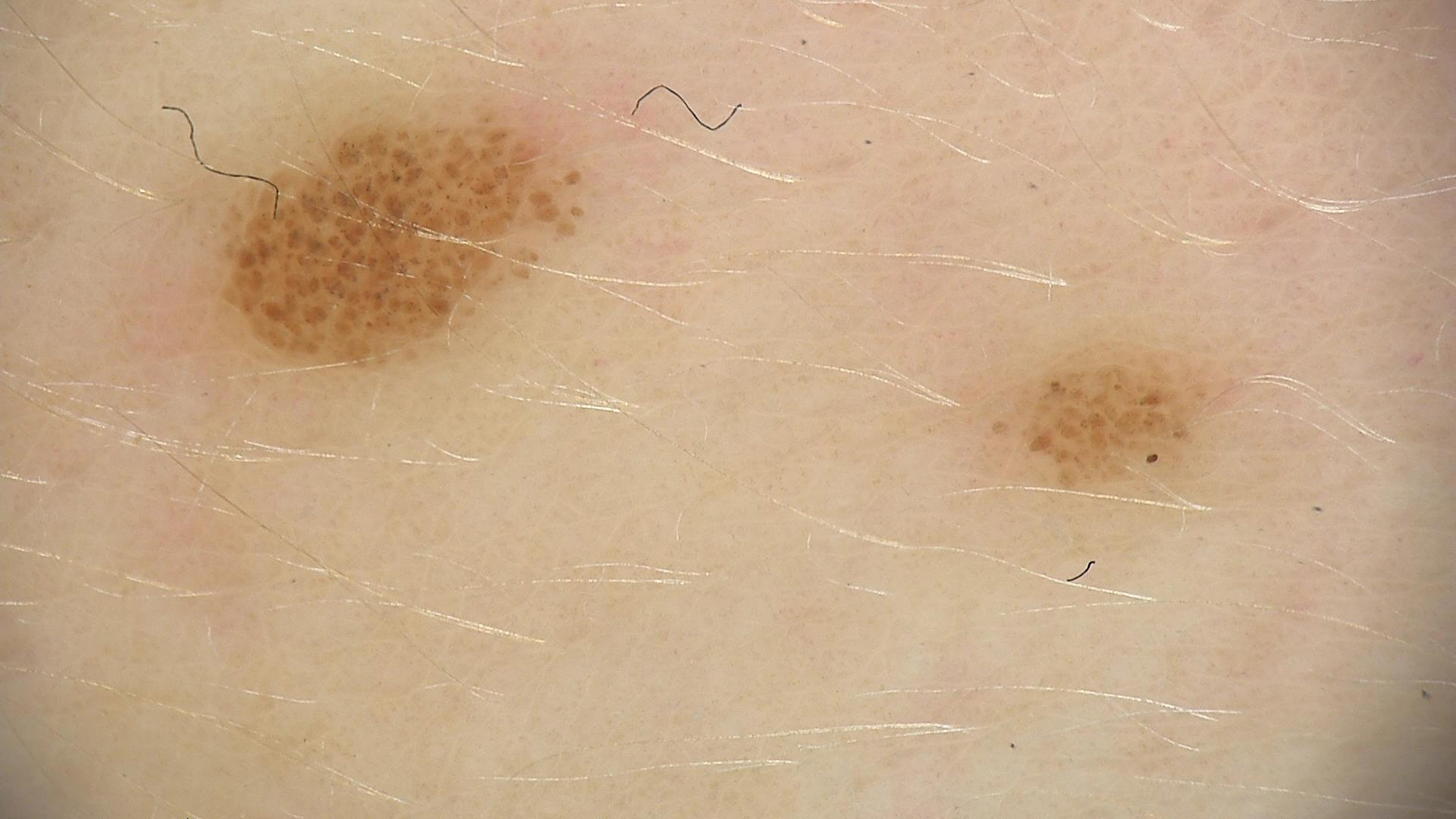image: dermoscopy | lesion type: banal | diagnosis: compound nevus (expert consensus).